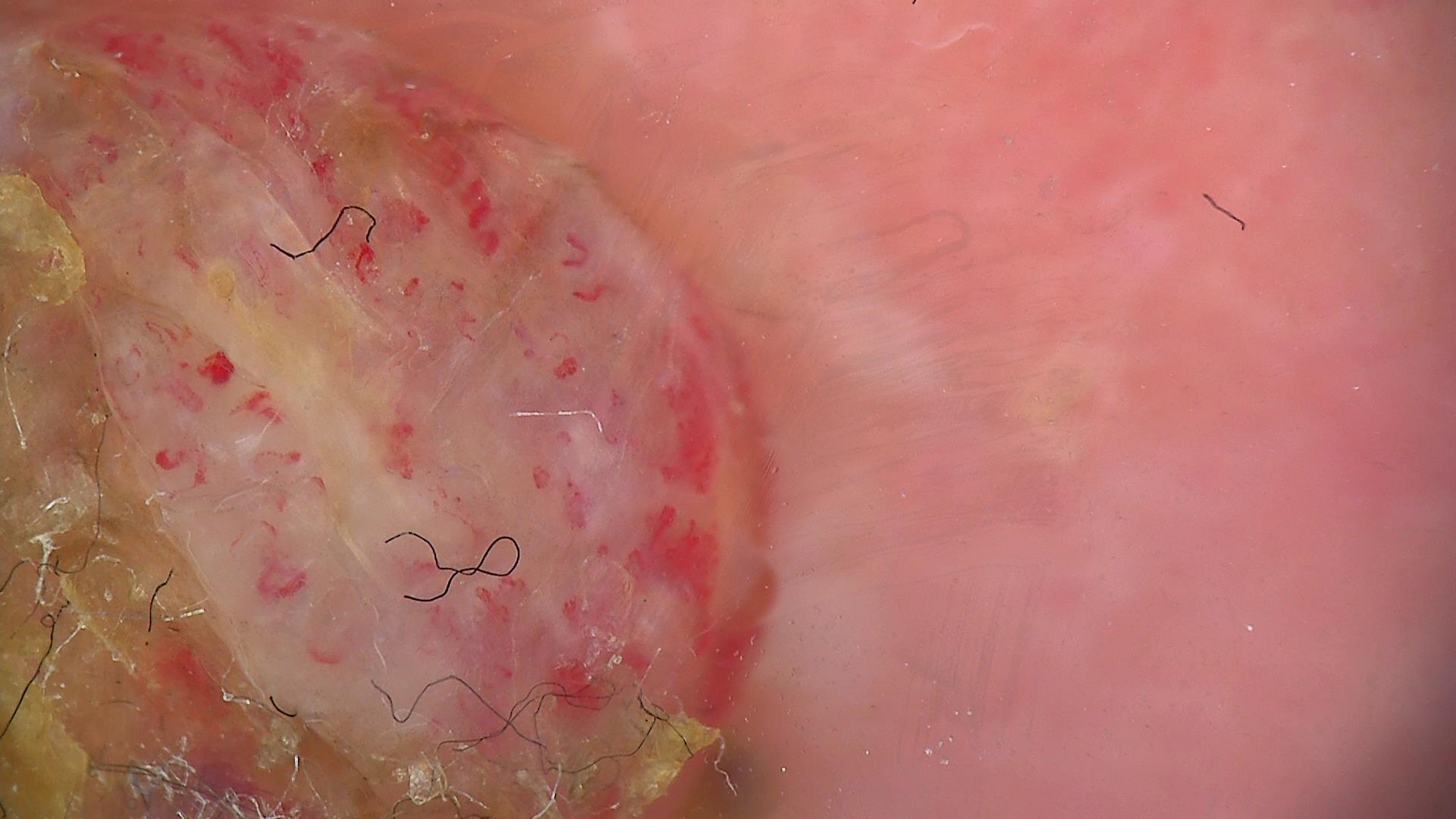Summary:
A dermoscopic close-up of a skin lesion.
Conclusion:
Histopathologically confirmed as a malignant, keratinocytic lesion — a squamous cell carcinoma.